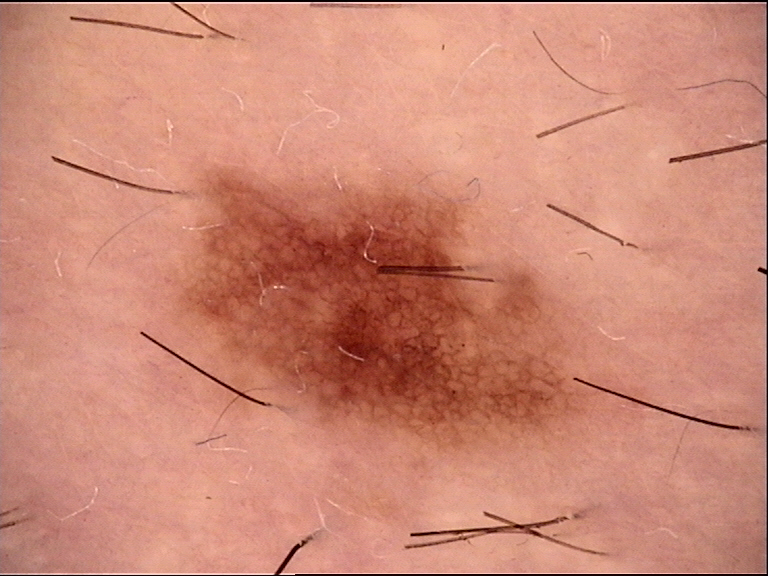| field | value |
|---|---|
| image type | dermoscopy |
| diagnosis | dysplastic junctional nevus (expert consensus) |